A skin lesion imaged with a dermatoscope · a female subject aged 23-27:
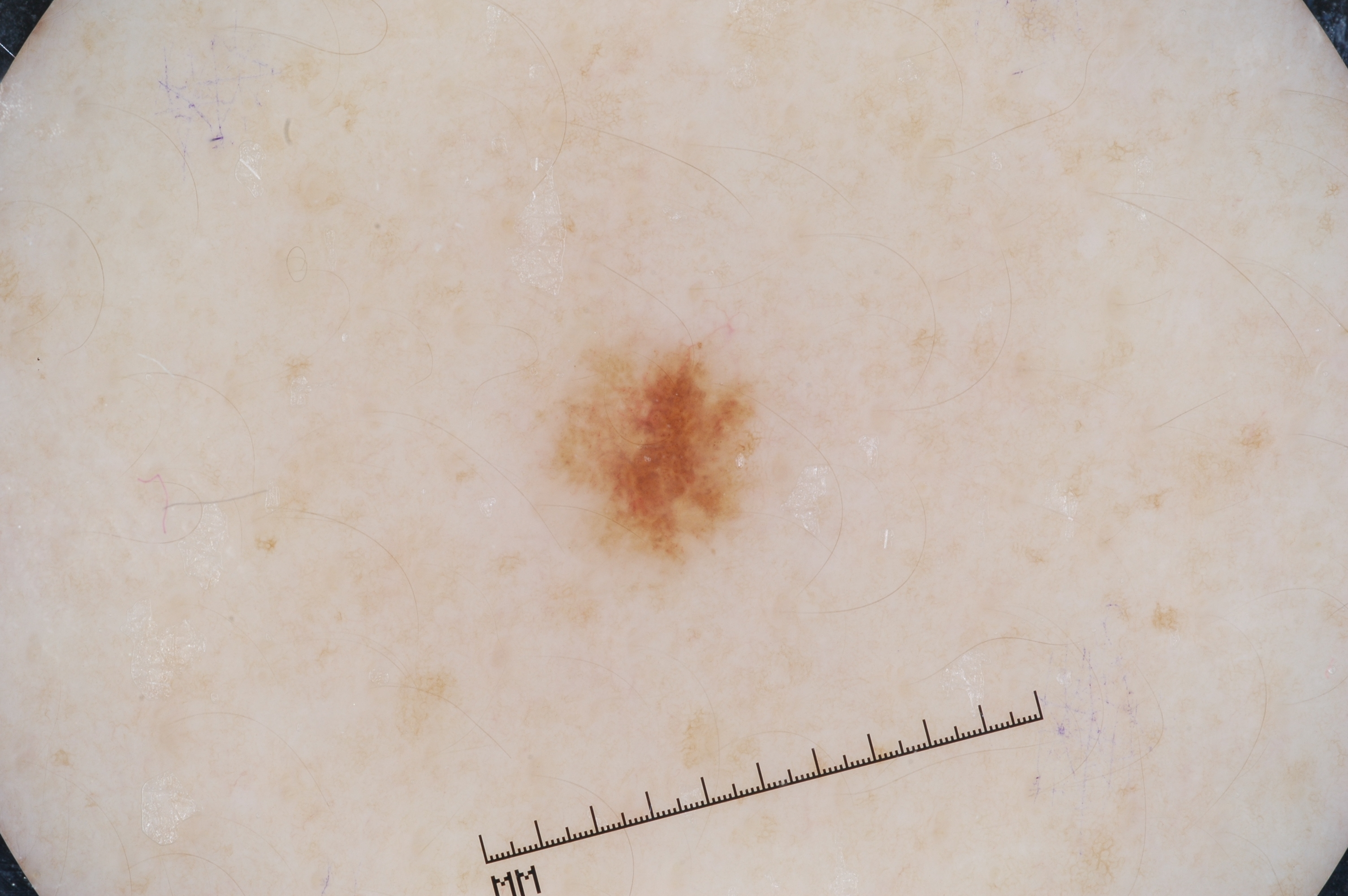The lesion occupies the region left=548, top=336, right=758, bottom=567. The lesion covers approximately 3% of the dermoscopic field. Dermoscopically, the lesion shows milia-like cysts and pigment network. The clinical diagnosis was a melanocytic nevus, a benign skin lesion.